The affected area is the head or neck, back of the torso, arm, leg, front of the torso and back of the hand · the subject is female · the photograph was taken at an angle.
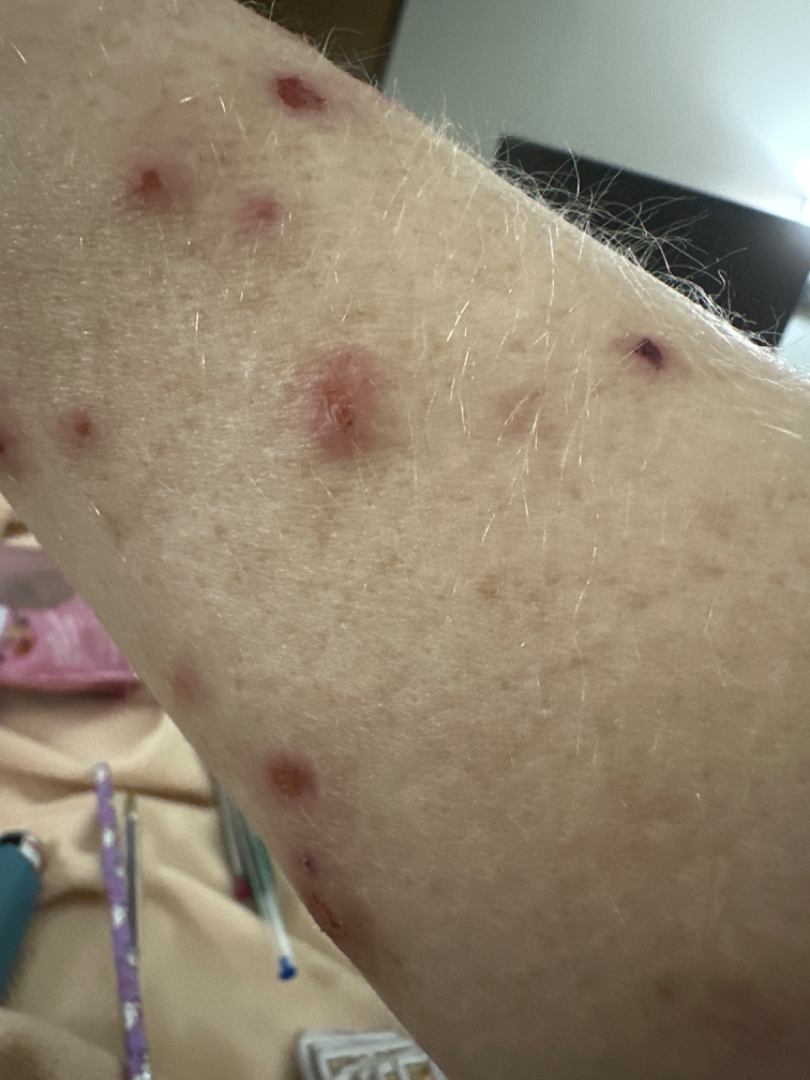<case>
  <differential>
    <leading>Prurigo</leading>
  </differential>
</case>